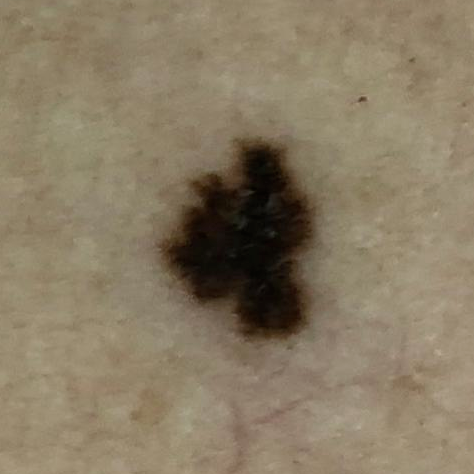{
  "diagnosis": {
    "name": "melanoma",
    "code": "MEL",
    "malignancy": "malignant",
    "confirmation": "histopathology"
  }
}